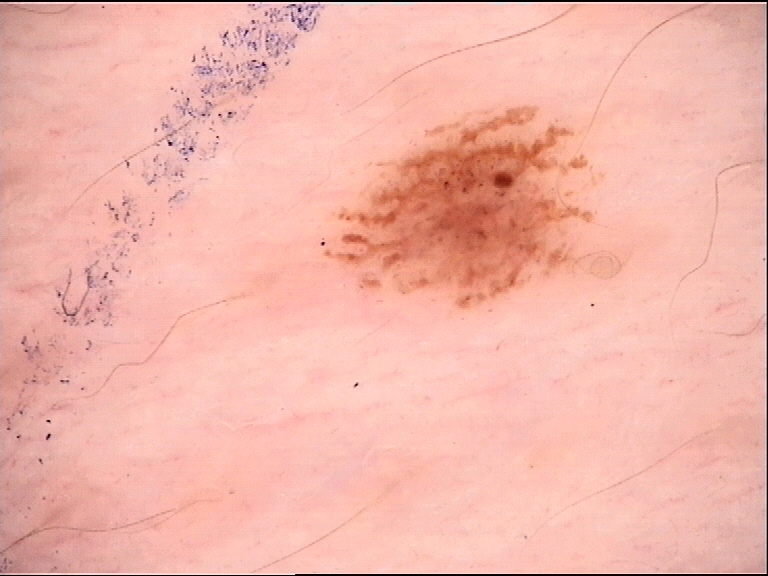modality: dermoscopy; diagnosis: dysplastic junctional nevus (expert consensus).